The patient says their skin reddens painfully with sun exposure; a dermoscopy image of a skin lesion — 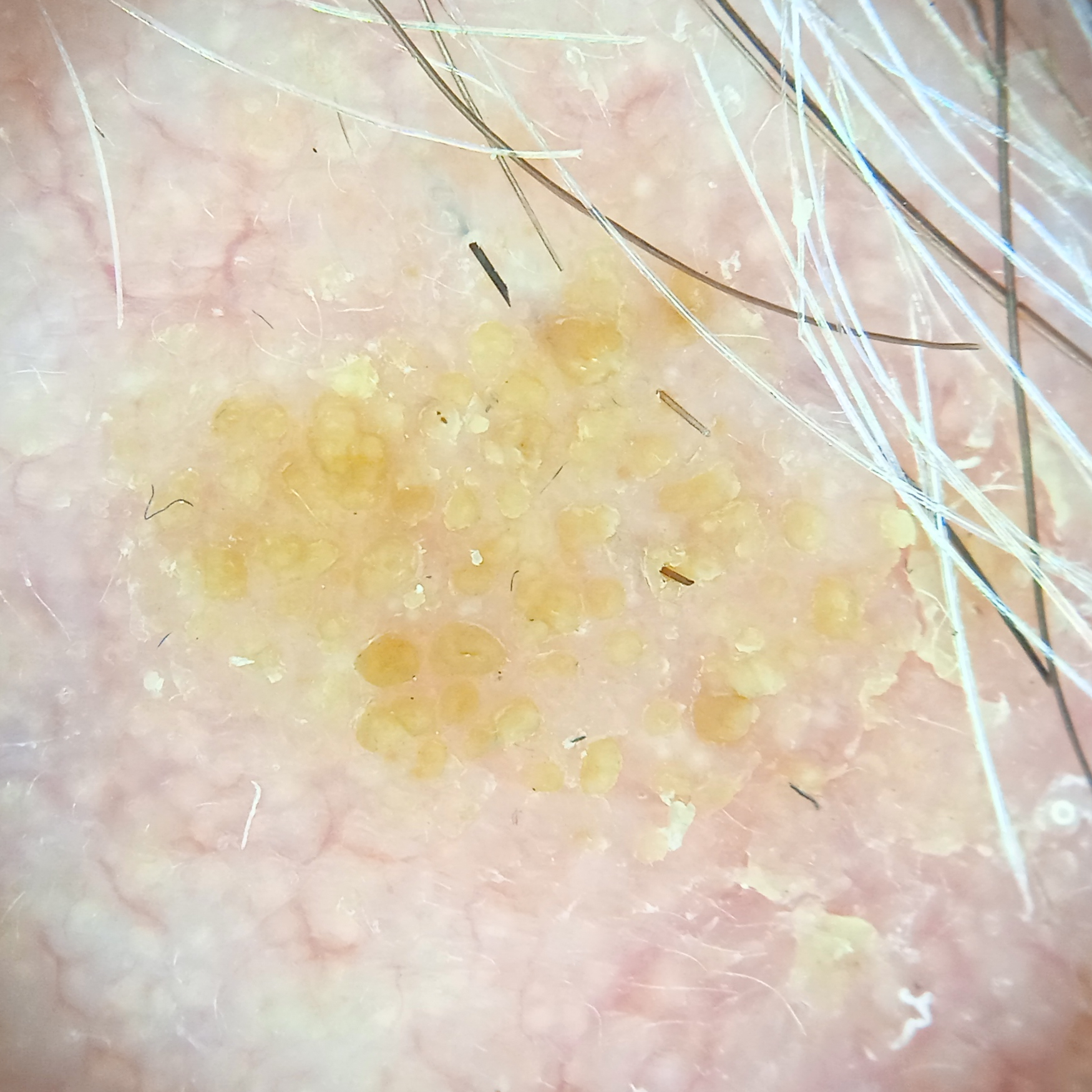<record>
<lesion_location>the face</lesion_location>
<diagnosis>
<name>seborrheic keratosis</name>
<malignancy>benign</malignancy>
</diagnosis>
</record>